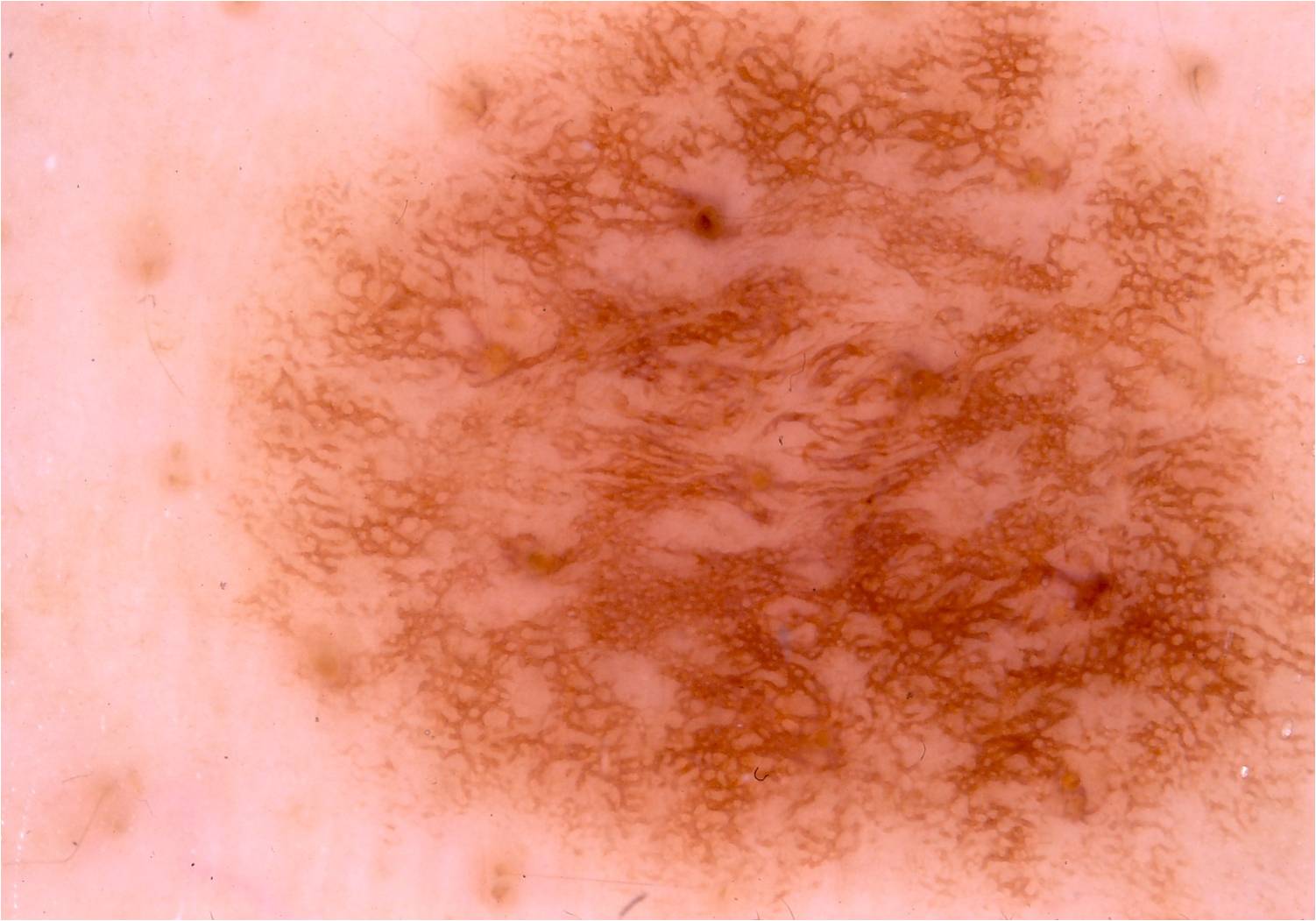{"image": {"modality": "dermoscopy"}, "lesion_location": {"bbox_xyxy": [216, 4, 1314, 919]}, "diagnosis": {"name": "melanocytic nevus", "malignancy": "benign", "lineage": "melanocytic", "provenance": "clinical"}}